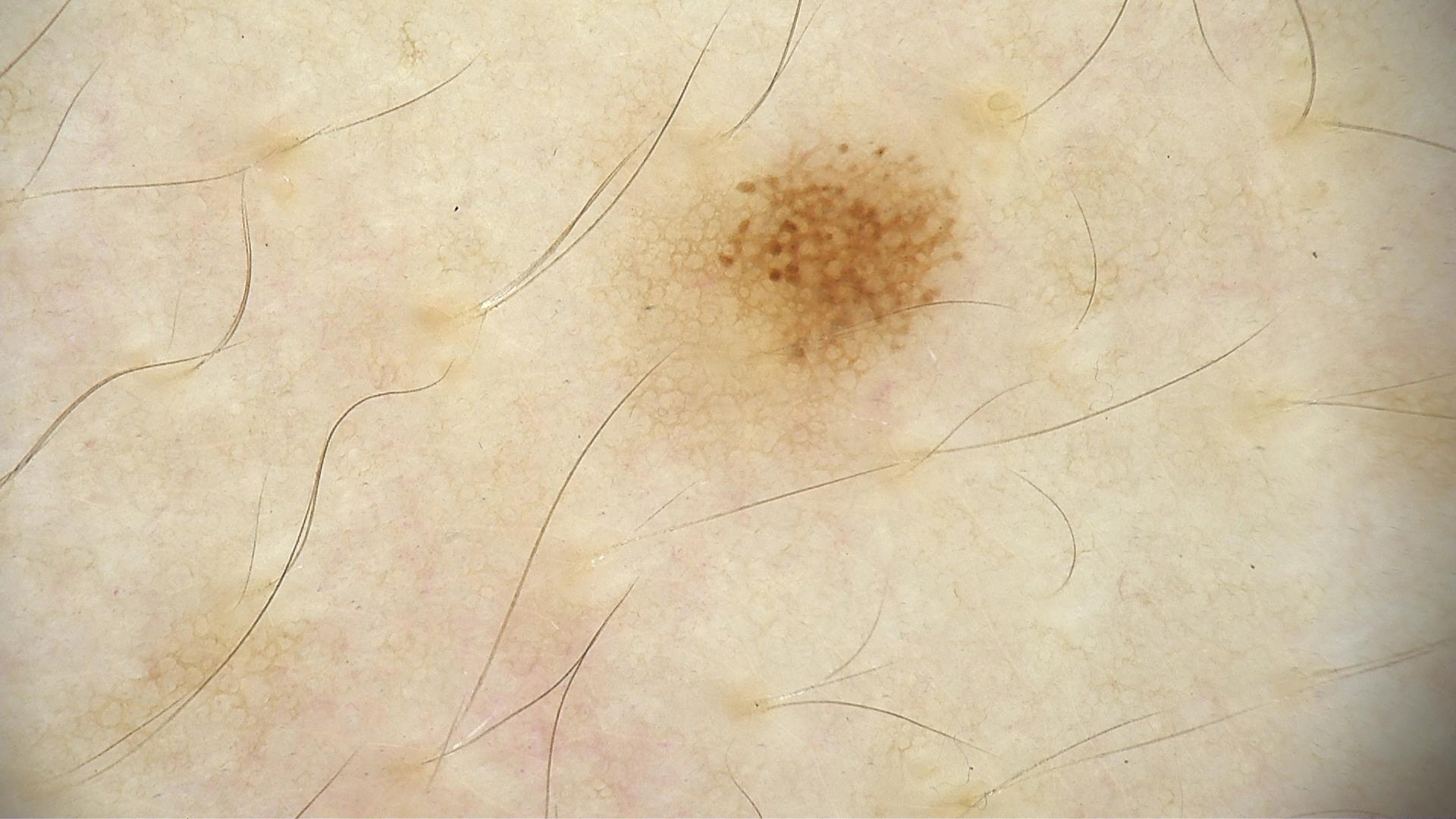imaging — dermatoscopy
diagnosis — dysplastic junctional nevus (expert consensus)